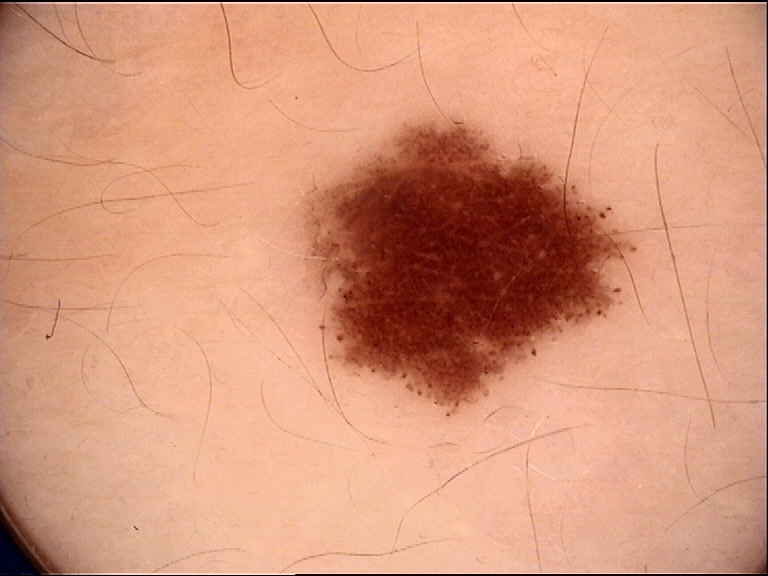image: dermoscopy
diagnosis:
  name: dysplastic junctional nevus
  code: jd
  malignancy: benign
  super_class: melanocytic
  confirmation: expert consensus